The affected area is the leg, the contributor is female, the photograph was taken at an angle:
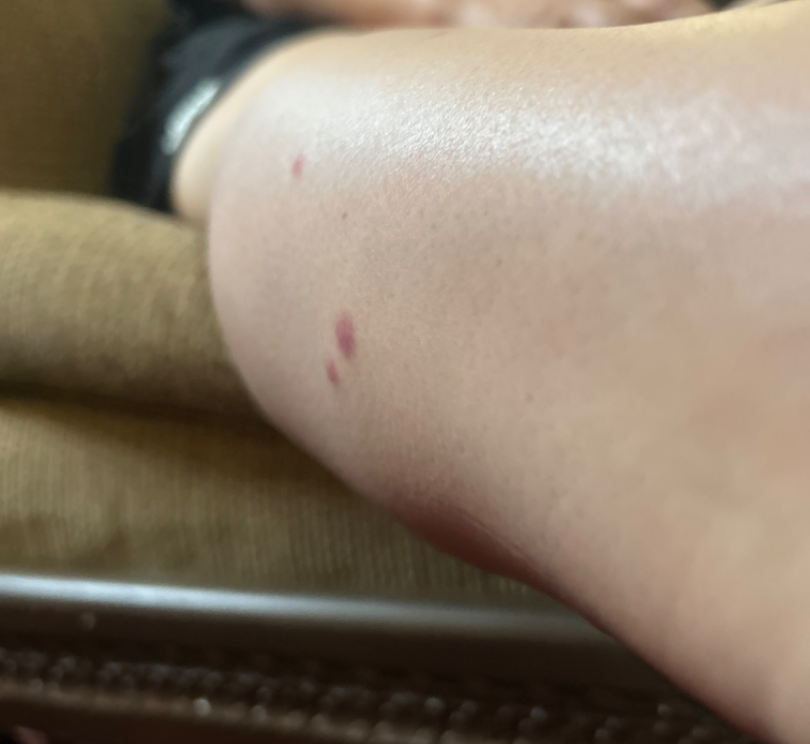{
  "symptoms": [
    "bothersome appearance",
    "burning"
  ],
  "texture": "raised or bumpy",
  "patient_category": "a rash",
  "duration": "less than one week",
  "differential": {
    "tied_lead": [
      "Insect Bite",
      "Leukocytoclastic Vasculitis"
    ]
  }
}